A patient 9 years old; a smartphone photograph of a skin lesion: 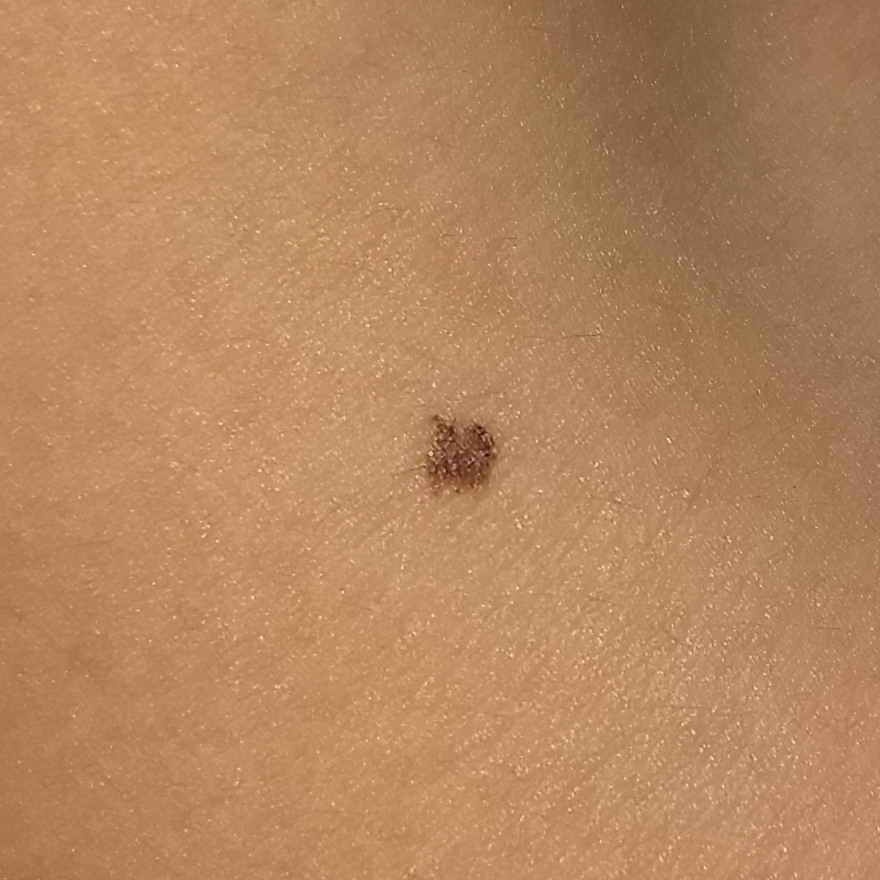Clinical context: The patient describes that the lesion has not bled. Conclusion: Consistent with a benign skin lesion — a nevus.